Dermoscopy of a skin lesion.
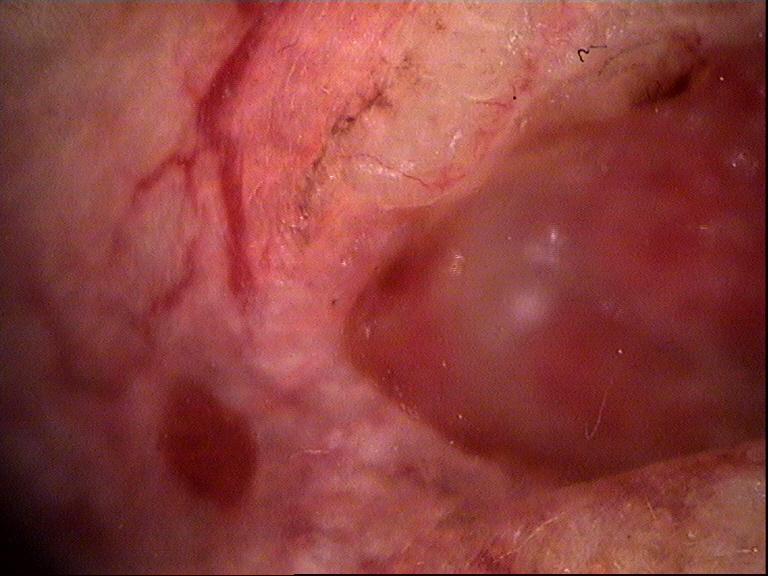Confirmed on histopathology as a malignant, keratinocytic lesion — a basal cell carcinoma.